A dermoscopy image of a single skin lesion.
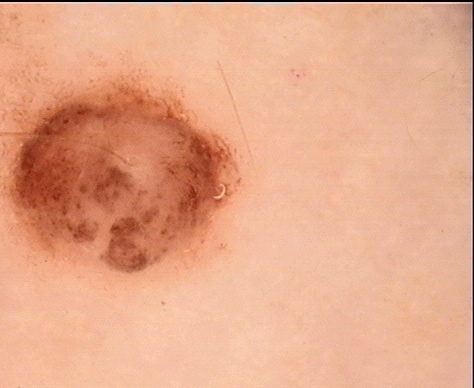{
  "lesion_type": {
    "main_class": "banal",
    "pattern": "dermal"
  },
  "diagnosis": {
    "name": "dermal nevus",
    "code": "db",
    "malignancy": "benign",
    "super_class": "melanocytic",
    "confirmation": "expert consensus"
  }
}